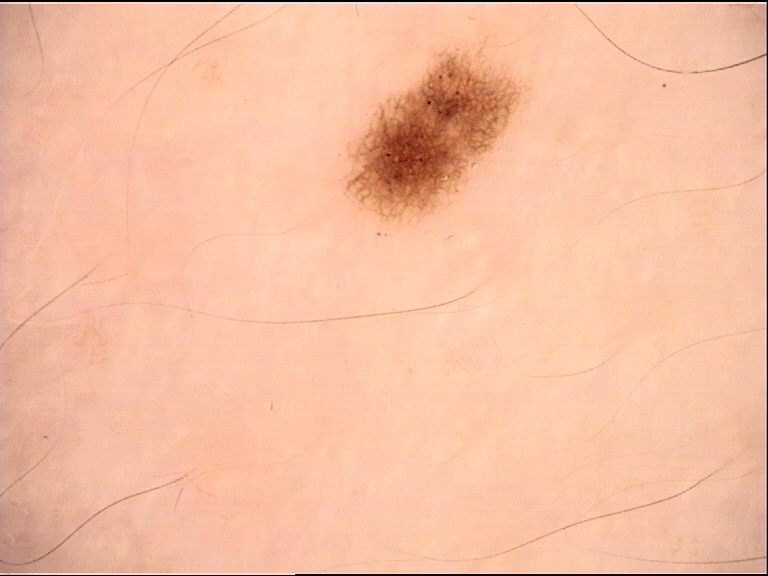imaging=dermoscopy | class=dysplastic junctional nevus (expert consensus).